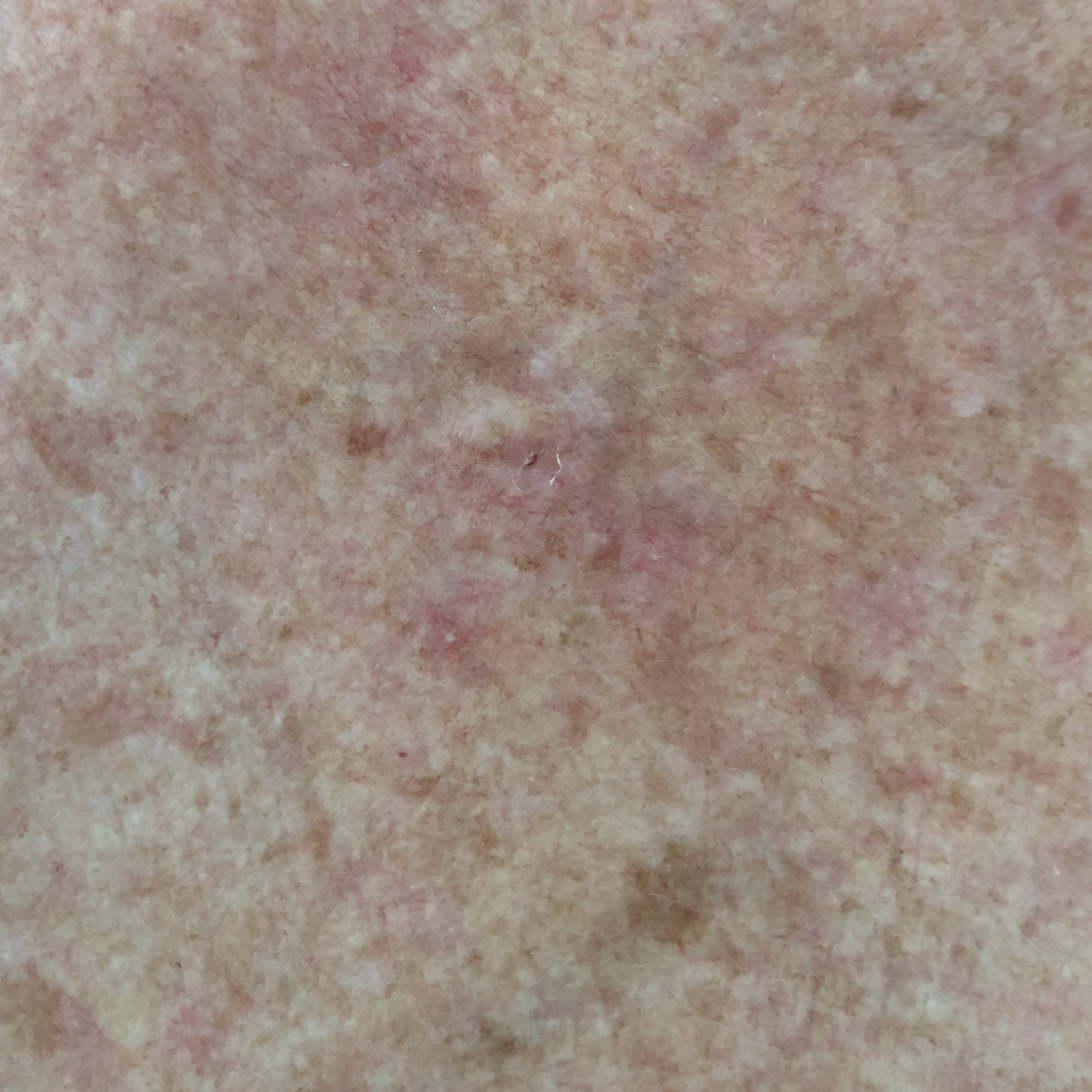modality — smartphone clinical photo
FST — III
patient — female, in their mid-50s
exposure history — prior malignancy (patient or family), alcohol use, prior skin cancer (patient or family)
body site — the chest
lesion diameter — 5x4 mm
patient-reported symptoms — itching / no bleeding, no change in appearance
assessment — actinic keratosis (clinical consensus)